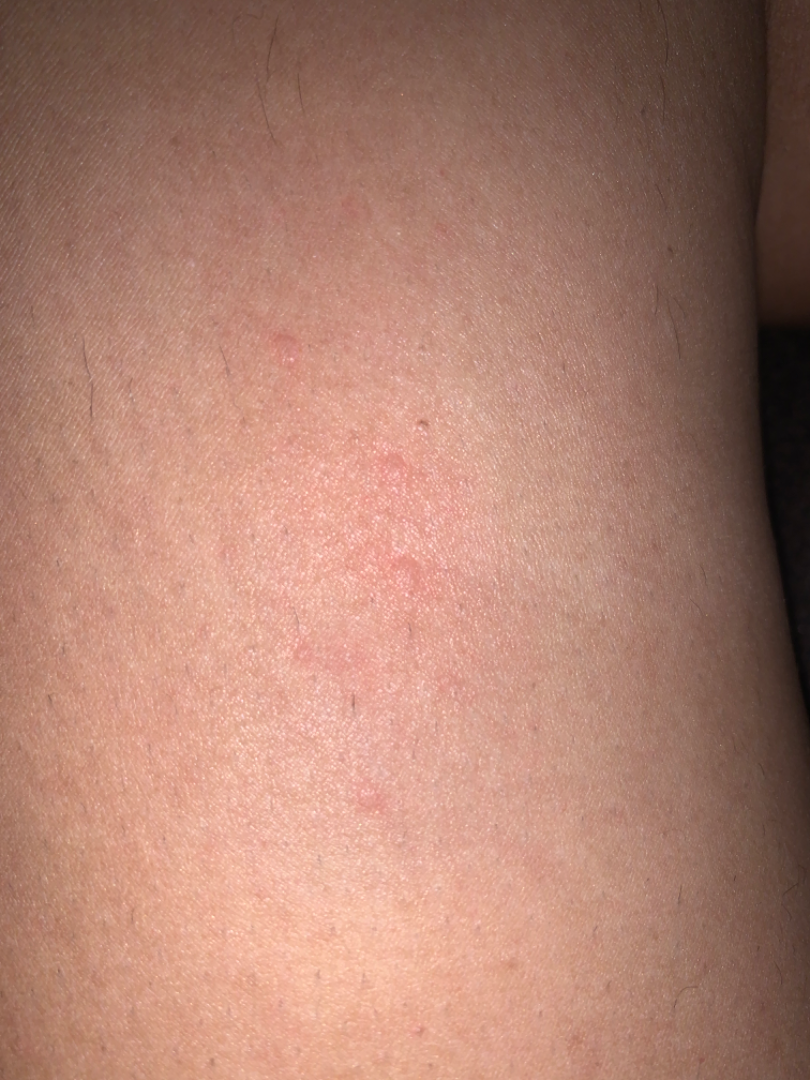This is a close-up image.
The leading consideration is Insect Bite; also raised was Allergic Contact Dermatitis.